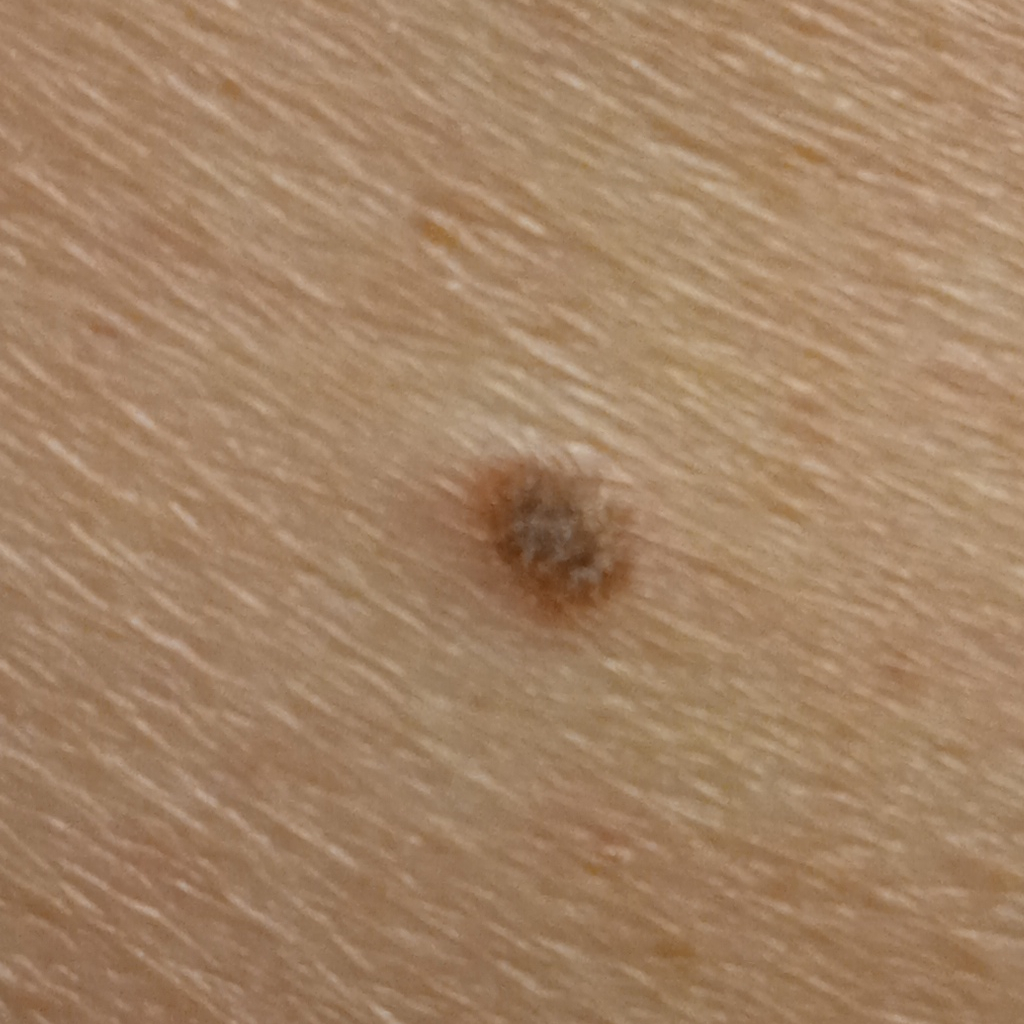referral=research study (no referral diagnosis) | patient=male, 79 years old | image type=clinical photo | diameter=5.9 mm | assessment=seborrheic keratosis (dermatologist consensus).